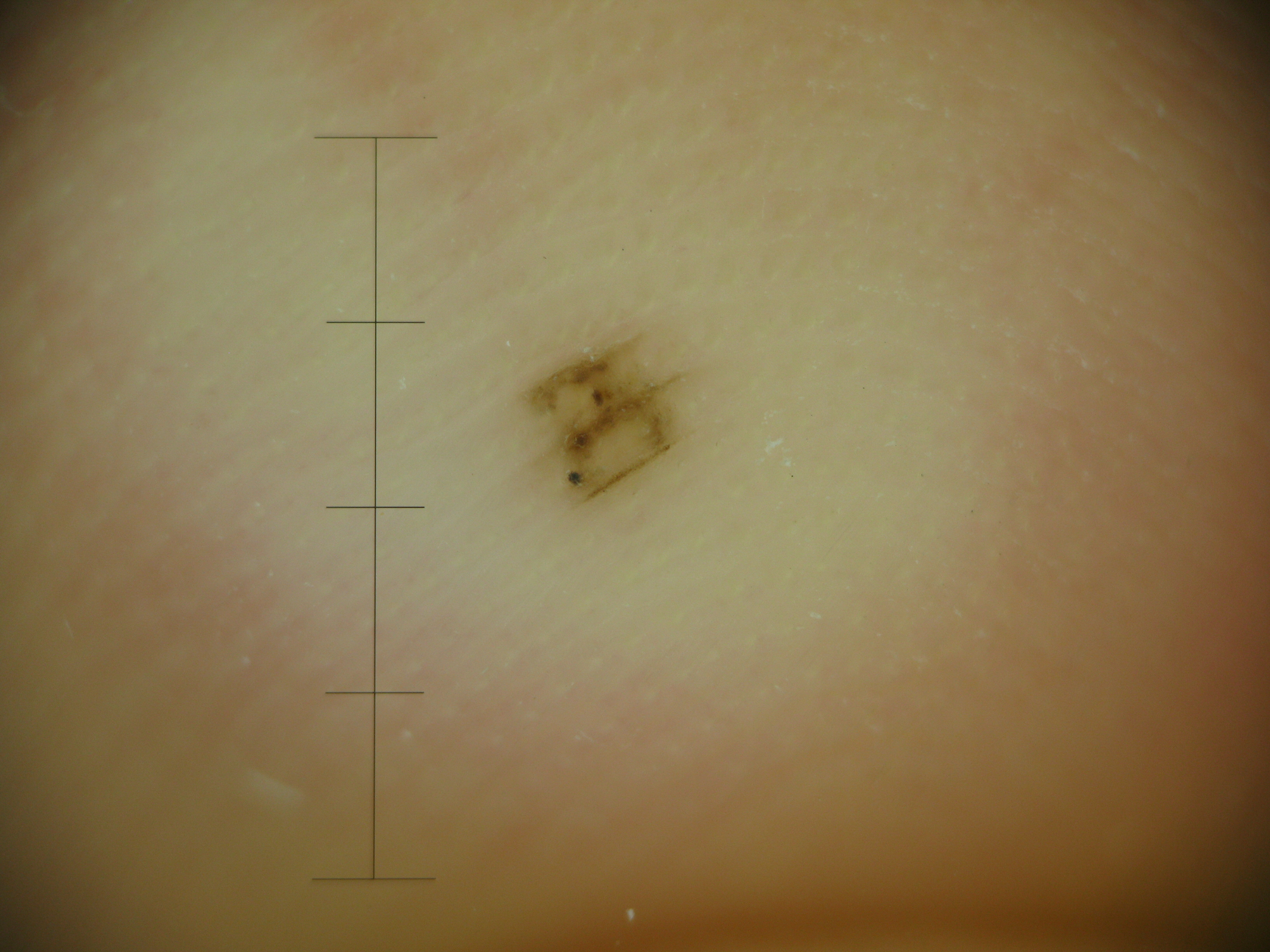A dermoscopic close-up of a skin lesion.
Diagnosed as a banal lesion — an acral junctional nevus.